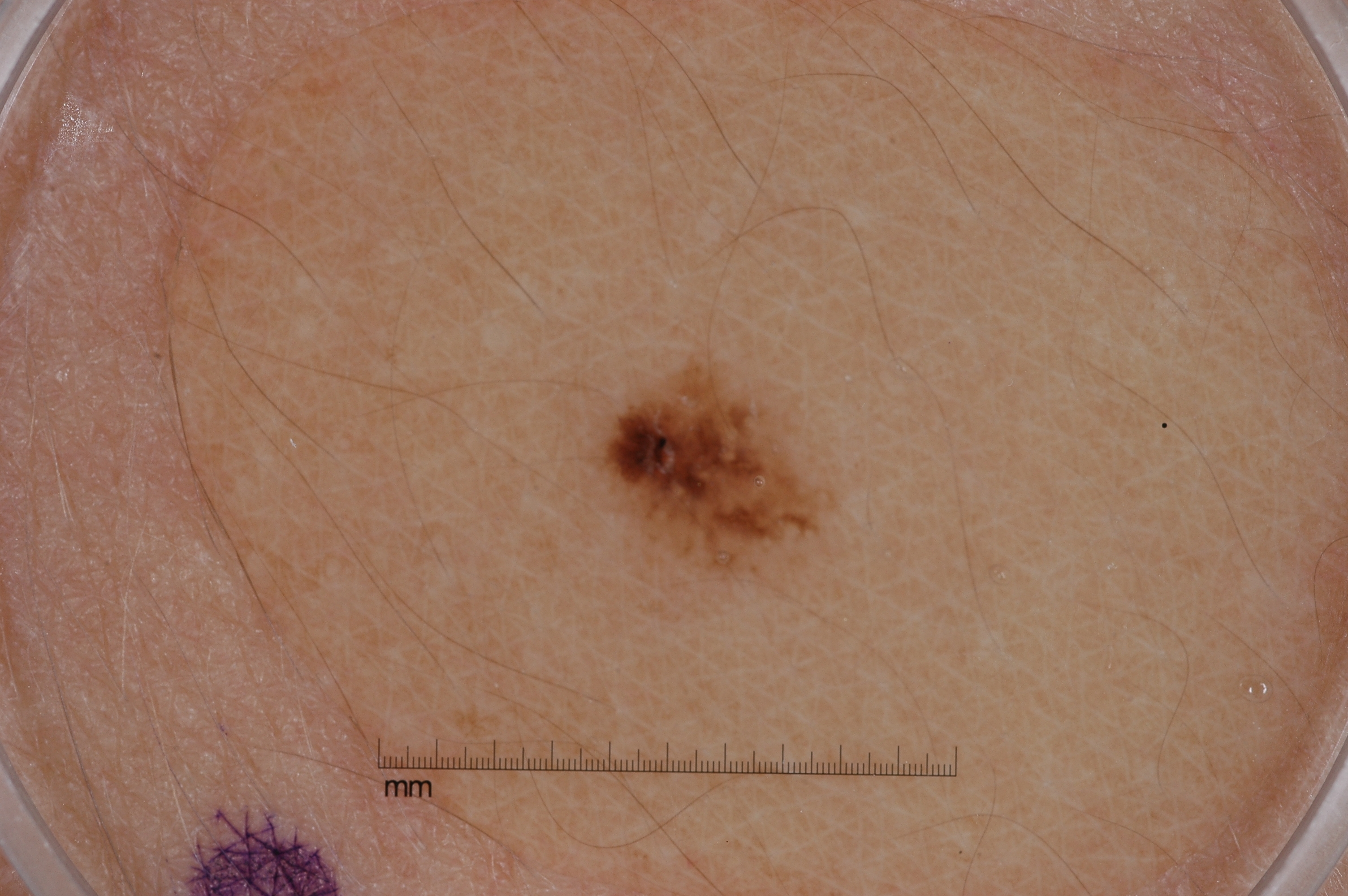Case summary: A dermoscopy image of a single skin lesion. Dermoscopic review identifies no pigment network, milia-like cysts, negative network, or streaks. In (x1, y1, x2, y2) order, the lesion spans (601, 371, 822, 574). The lesion is small relative to the field of view. Impression: The diagnostic assessment was a melanocytic nevus.